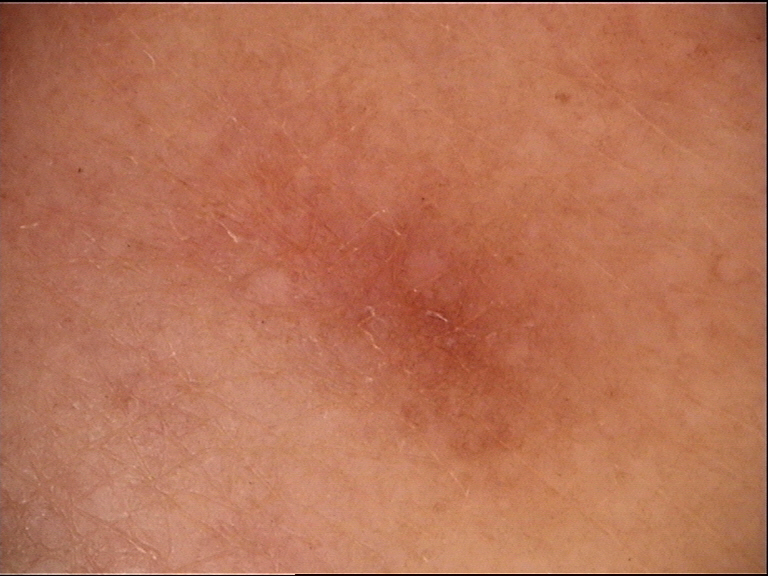{"diagnosis": {"name": "dermatofibroma", "code": "df", "malignancy": "benign", "super_class": "non-melanocytic", "confirmation": "expert consensus"}}